Located on the arm. Present for less than one week. The lesion is described as raised or bumpy. Self-categorized by the patient as a rash. The subject is female. Close-up view: 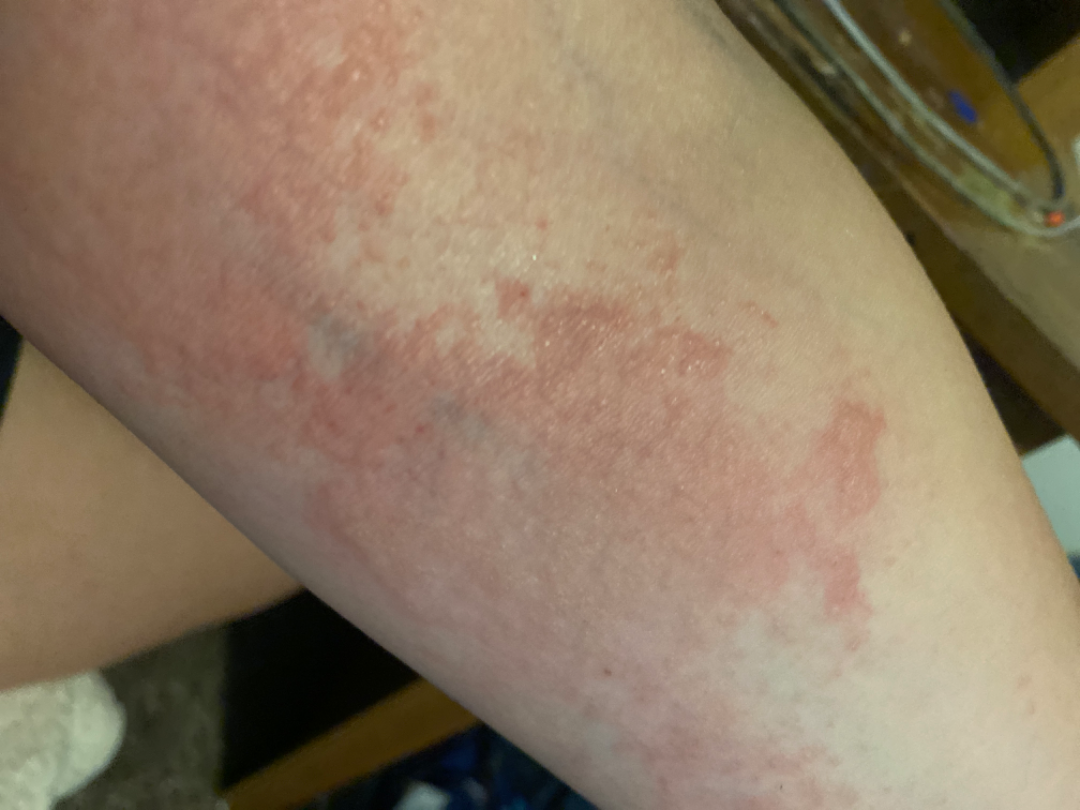Q: What is the dermatologist's impression?
A: the leading impression is Eczema; an alternative is Urticaria; possibly Psoriasis